A dermoscopy image of a single skin lesion; the patient is a male about 70 years old:
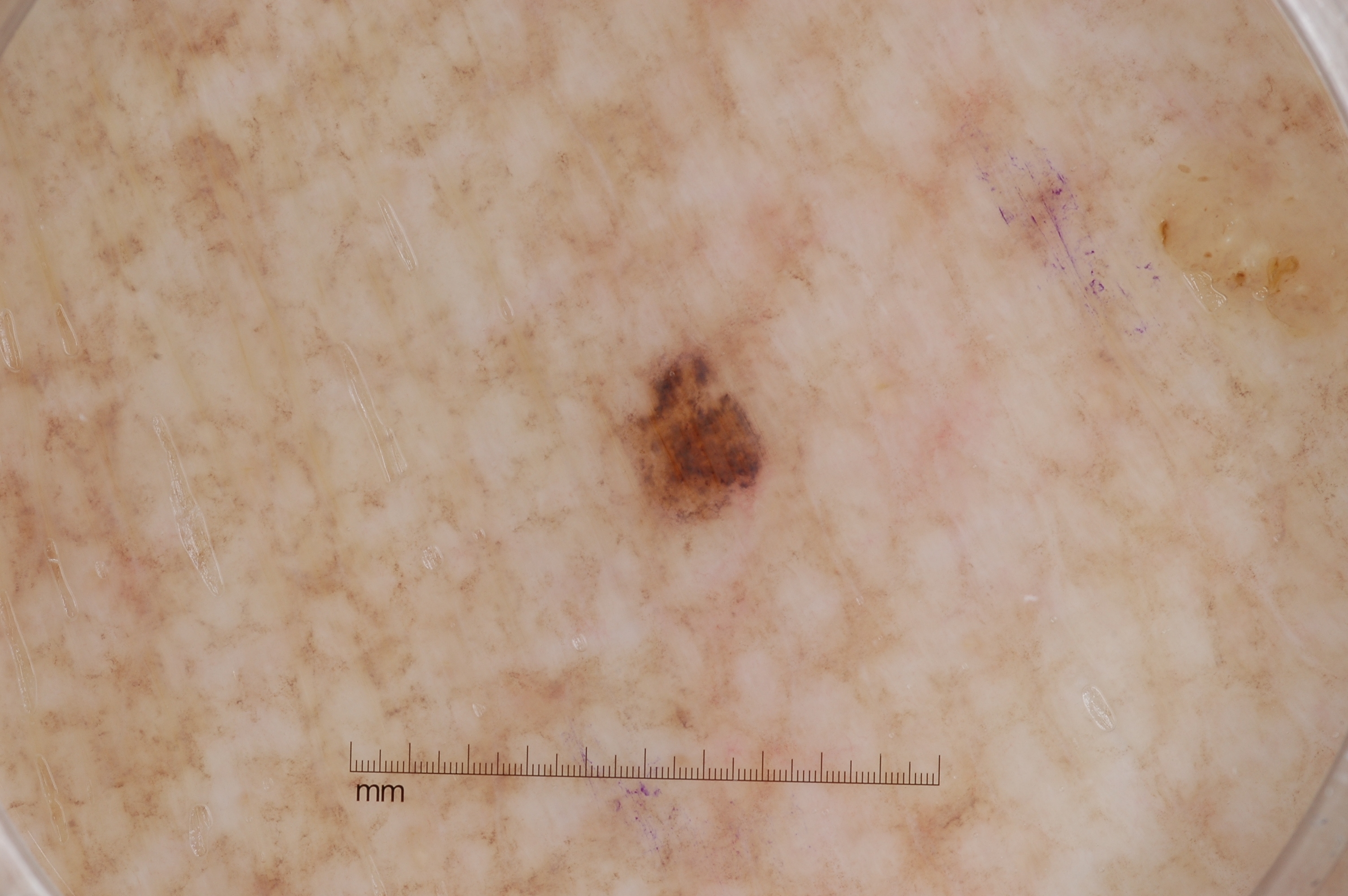The lesion spans left=611, top=336, right=779, bottom=532. A small lesion within a wider field of skin. Dermoscopic review identifies no negative network, milia-like cysts, streaks, or pigment network. Biopsy-confirmed as a melanoma, a malignancy.